A female subject 81 years of age · imaged for a research study, with no referral diagnosis recorded · a macroscopic clinical photograph of a skin lesion.
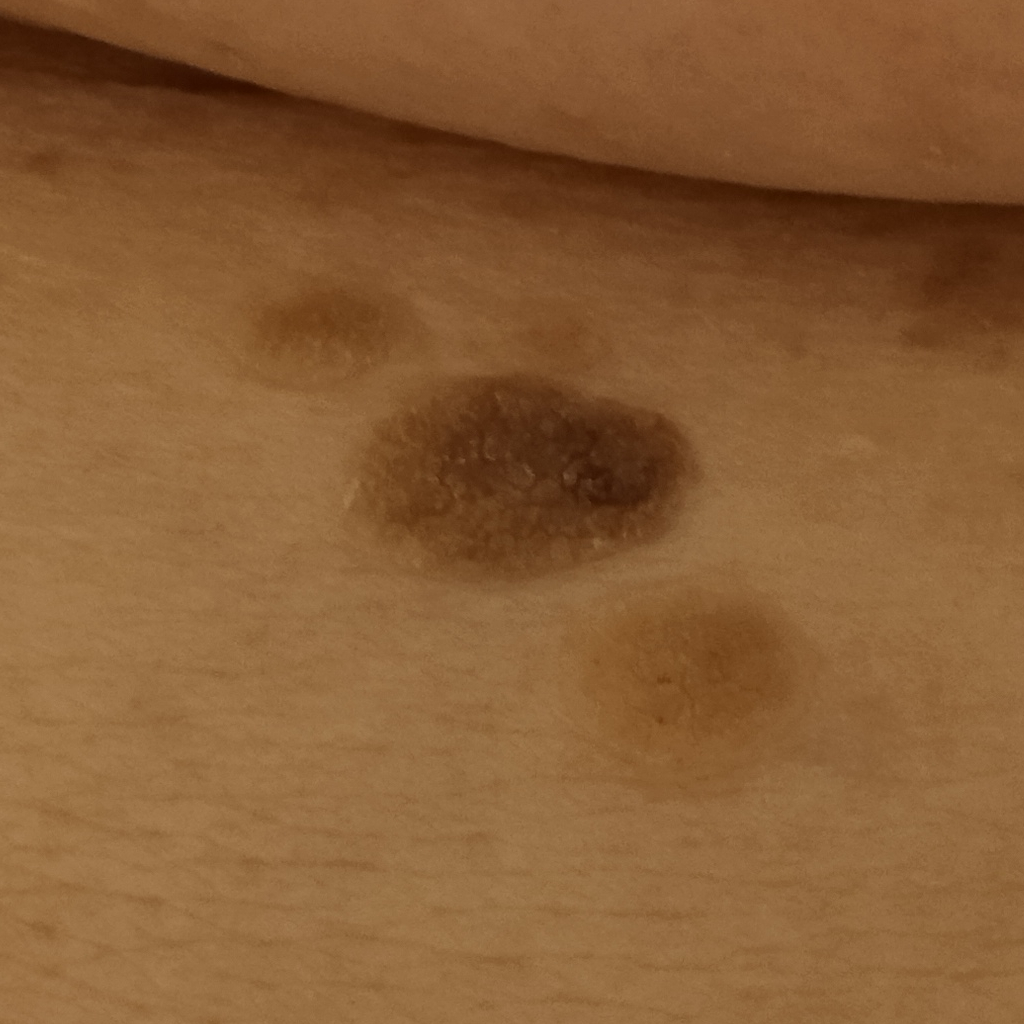The lesion was assessed as a seborrheic keratosis.